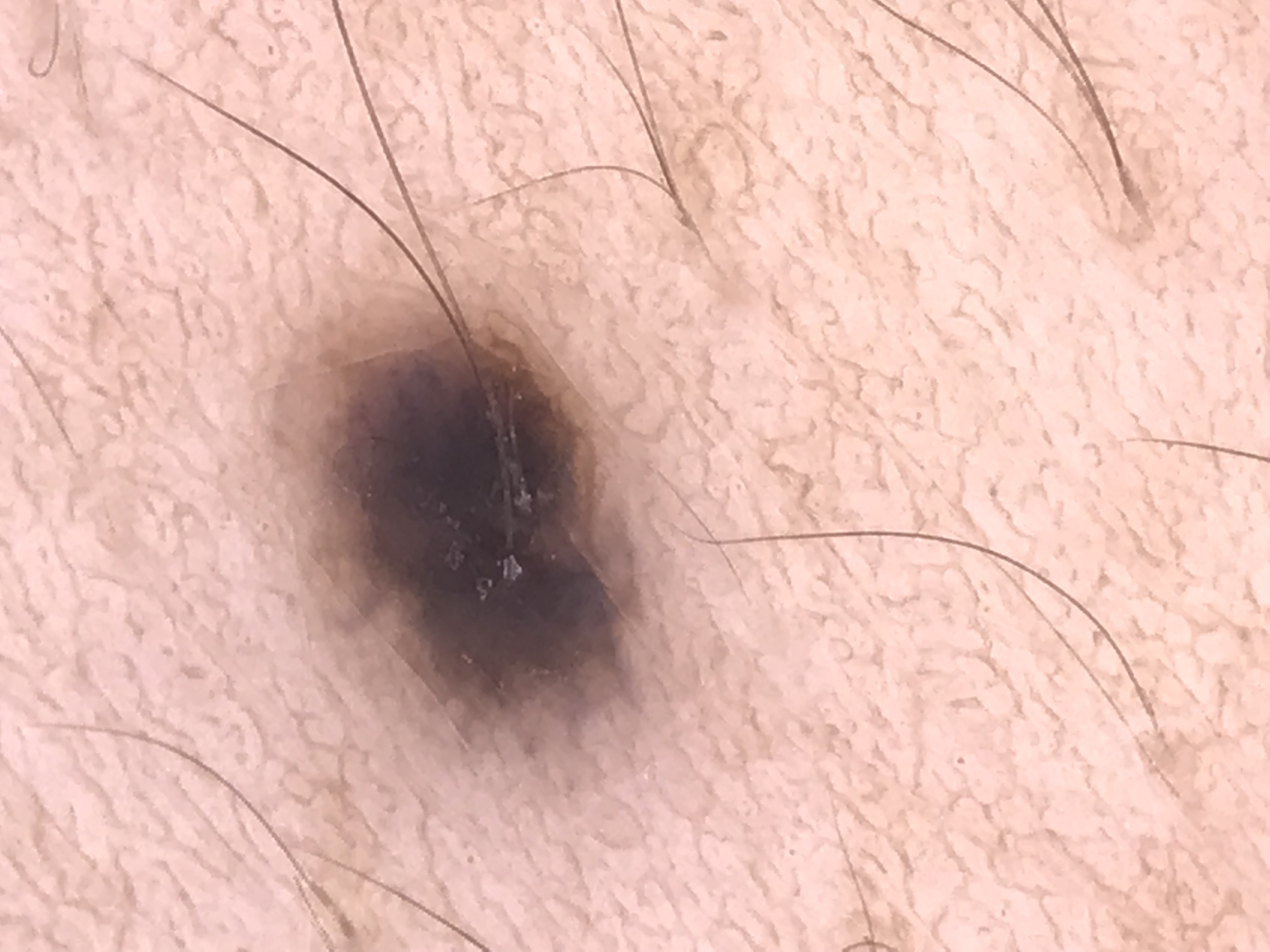A dermatoscopic image of a skin lesion. The morphology is that of a banal, dermal lesion. Classified as a blue nevus.